The subject is 18–29, female. This is a close-up image. Reported lesion symptoms include enlargement and itching. The patient considered this a rash. The lesion involves the front of the torso and back of the torso. Reported duration is one to four weeks. The patient indicates the lesion is rough or flaky: 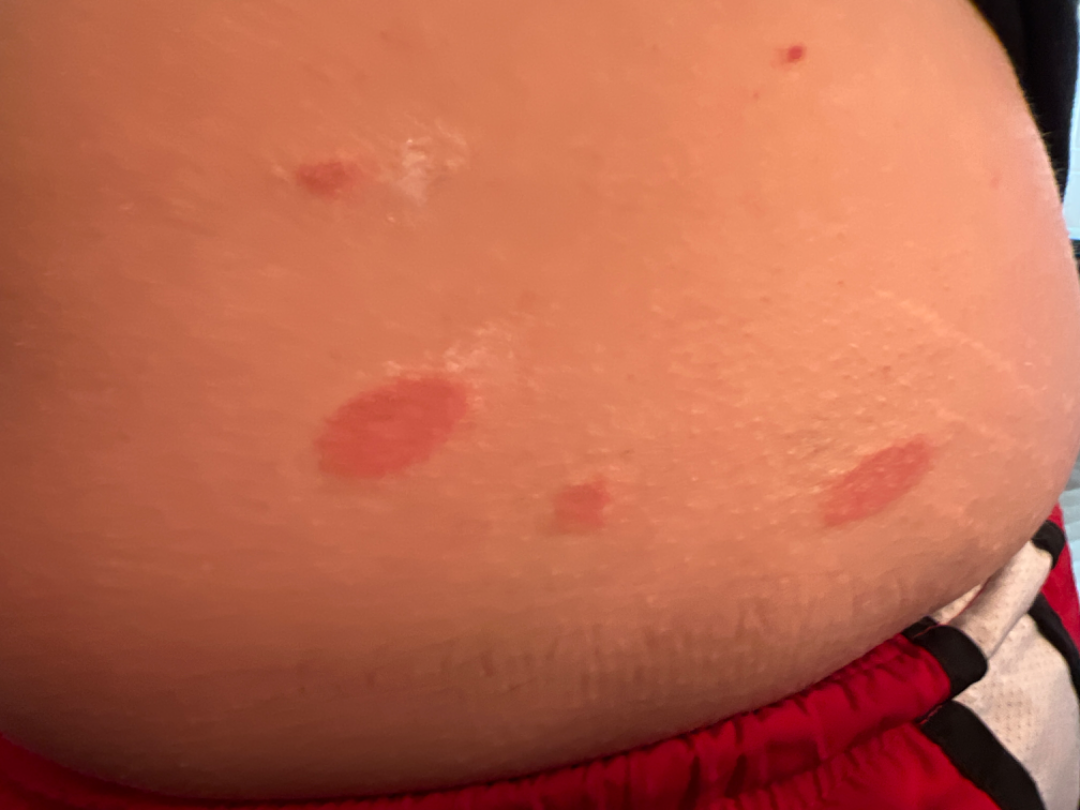The reviewing dermatologist was unable to assign a differential diagnosis from the image.